An image taken at an angle. Female patient, age 18–29:
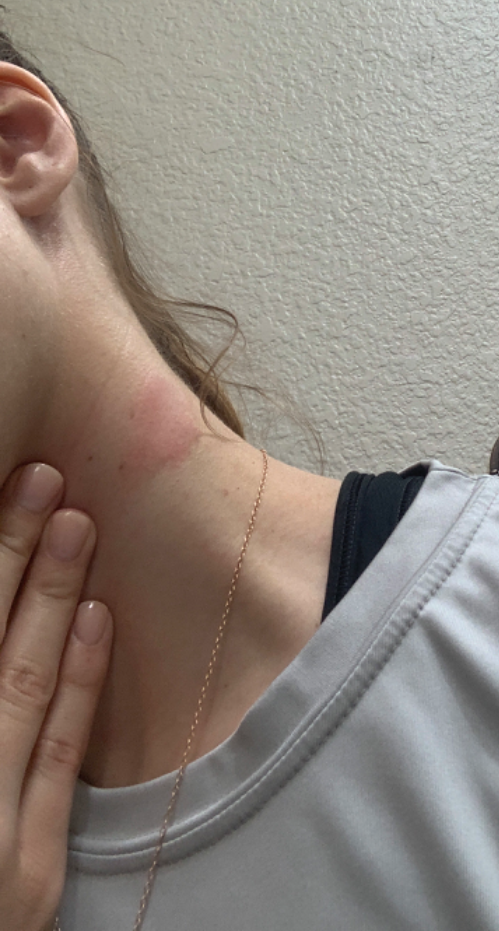impression: the differential, in no particular order, includes Urticaria and Allergic Contact Dermatitis.